A dermoscopy image of a single skin lesion: 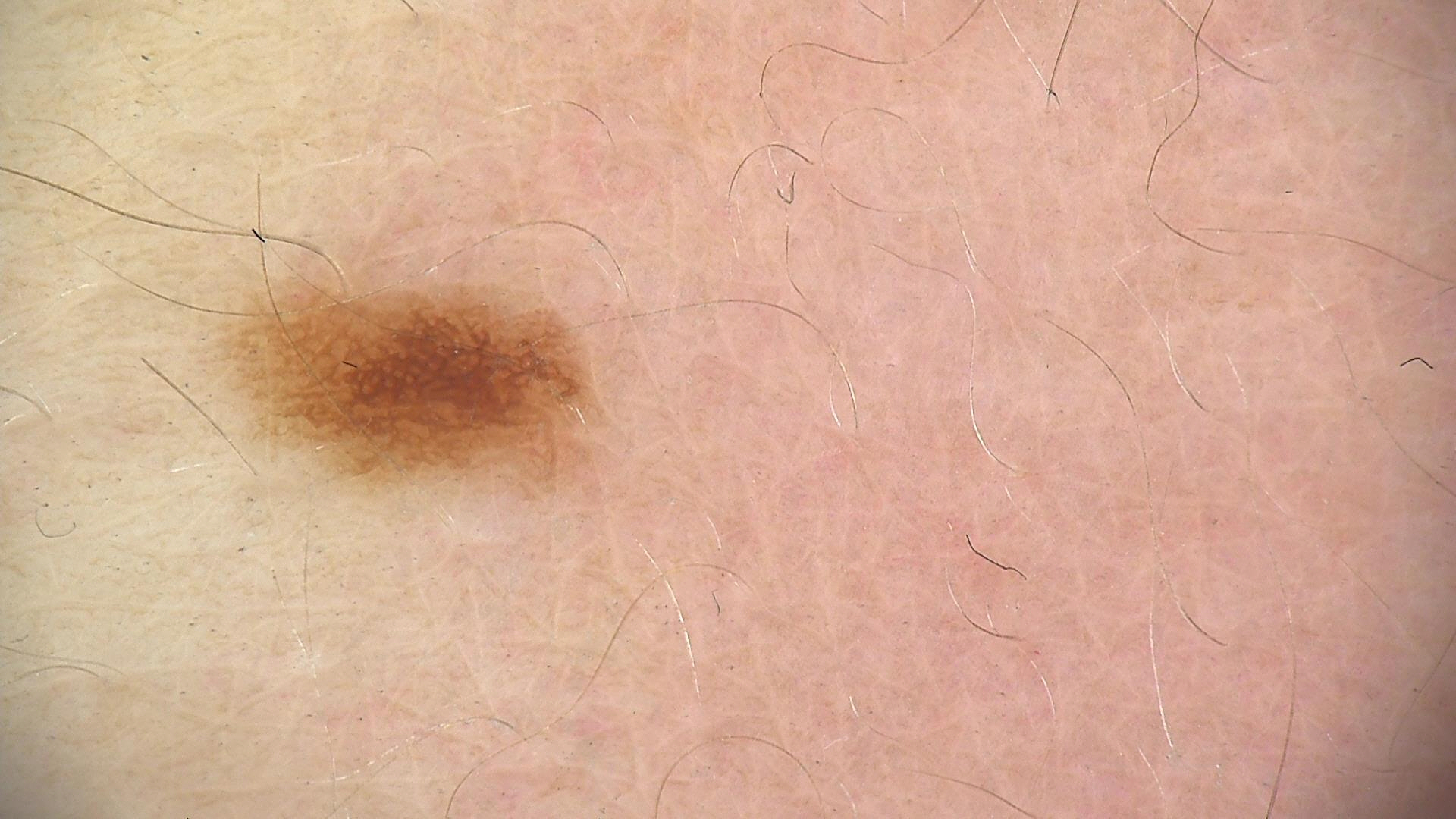class: dysplastic junctional nevus (expert consensus).